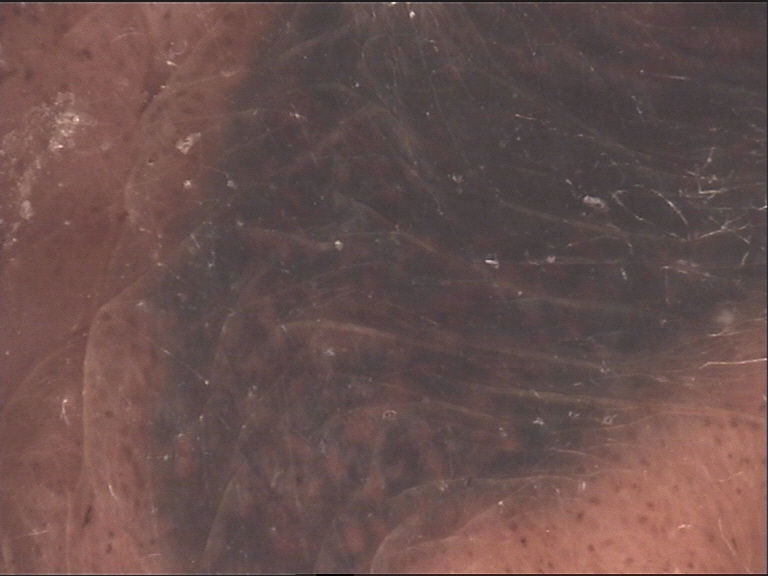Summary: A dermoscopic close-up of a skin lesion. Impression: Diagnosed as a banal lesion — a congenital compound nevus.